A clinical photograph of a skin lesion; a subject age 52.
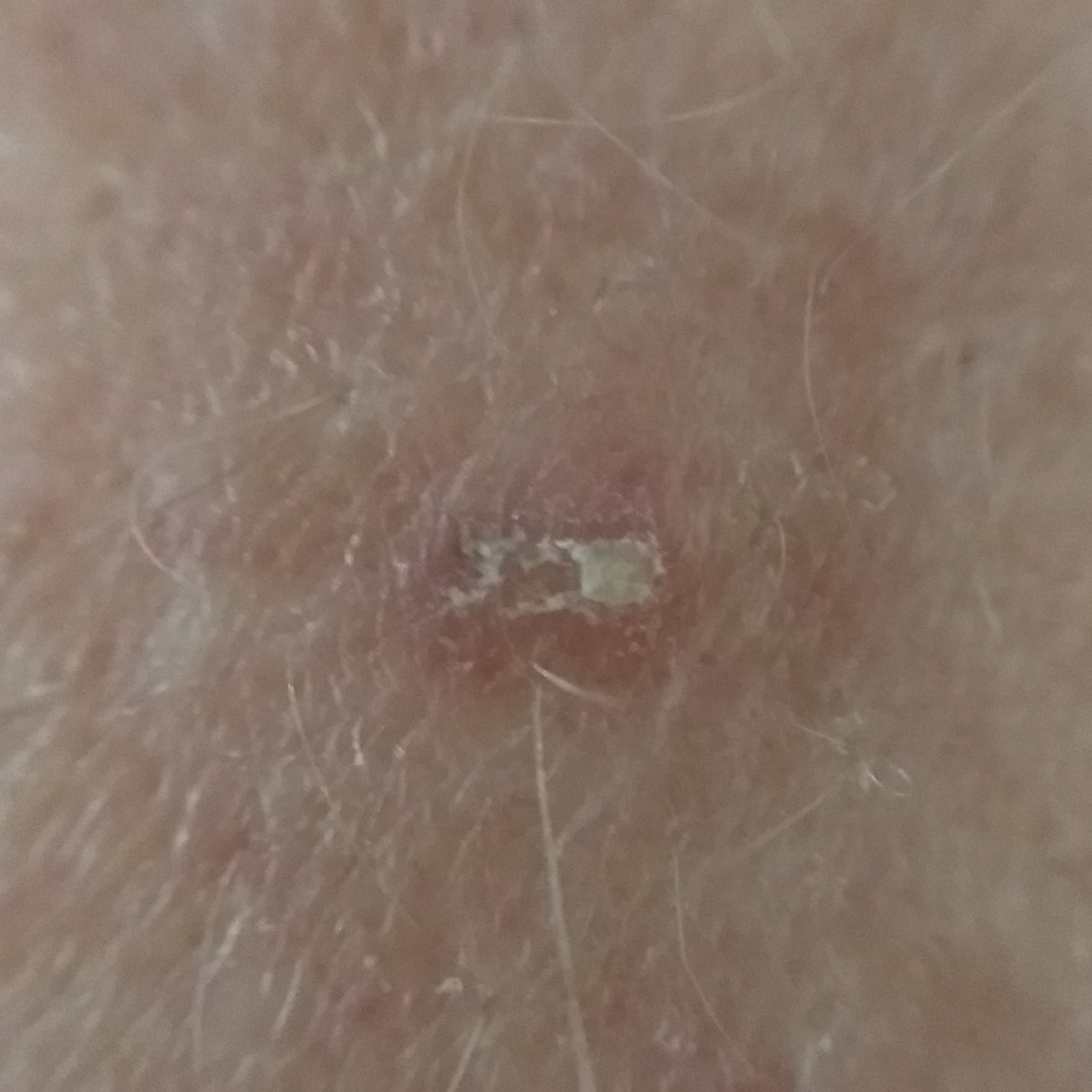Notes:
– site: a forearm
– diagnosis: actinic keratosis (clinical consensus)